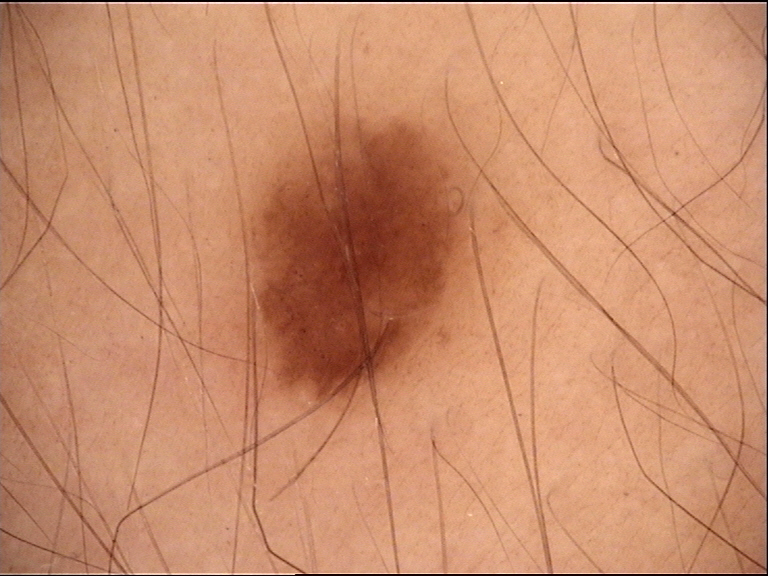Dermoscopy of a skin lesion. Labeled as a banal lesion — a junctional nevus.